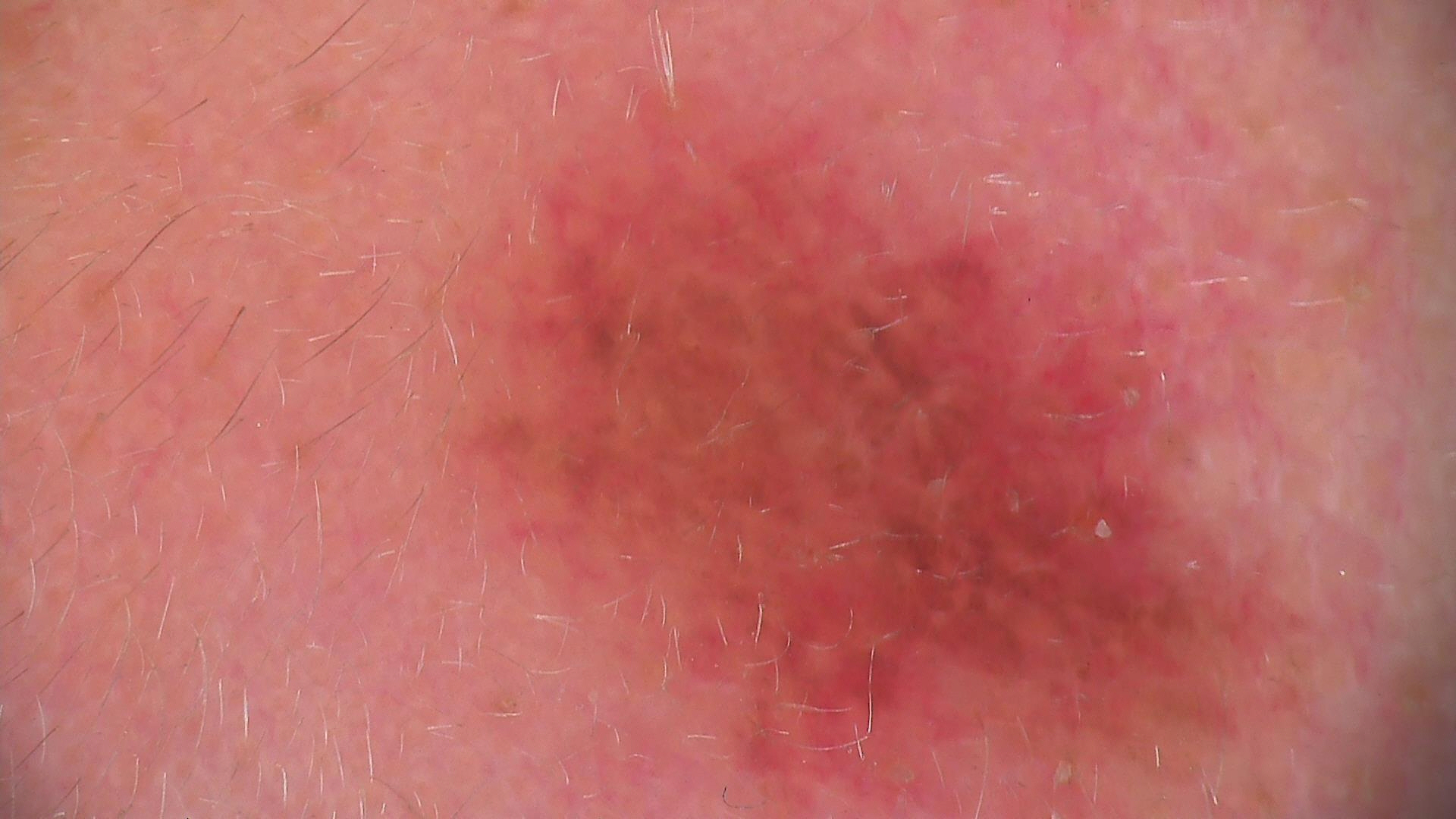Q: What kind of image is this?
A: dermatoscopy
Q: What is the diagnosis?
A: dysplastic junctional nevus (expert consensus)